Acquired for a research image collection, with no referral diagnosis; on a questionnaire the patient reported a personal history of skin cancer and a personal history of cancer; a male patient aged 76; the patient describes having few moles overall — 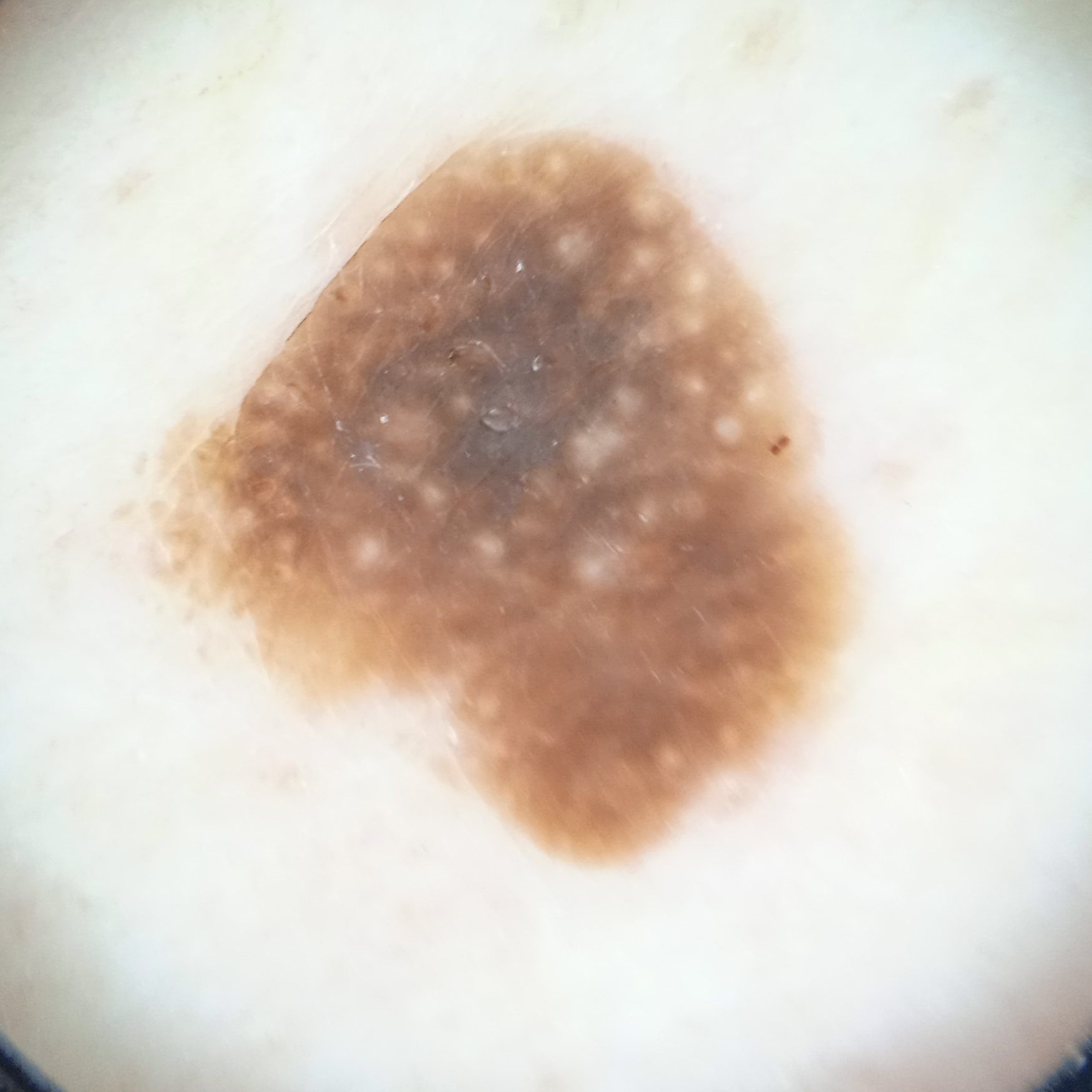Measuring roughly 8.6 mm.
The consensus diagnosis for this lesion was a seborrheic keratosis.